A dermoscopy image of a single skin lesion:
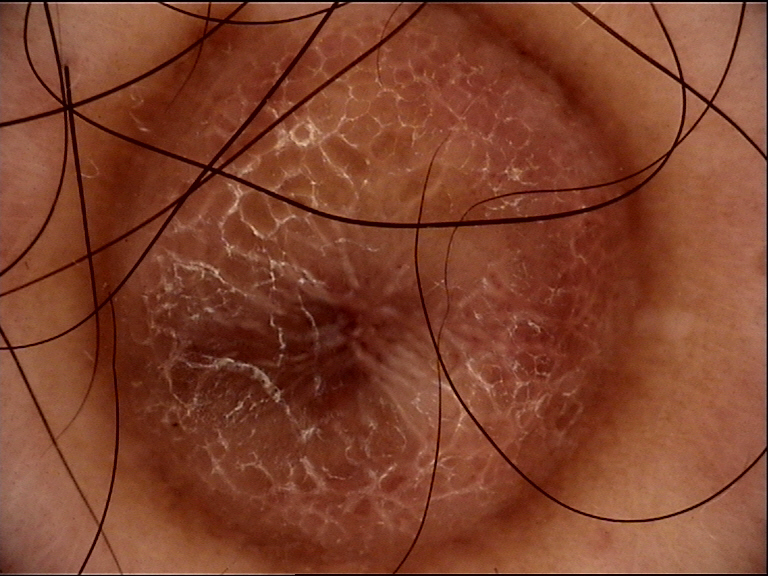assessment: dermatofibroma (expert consensus)